Dermoscopy of a skin lesion; a male patient about 65 years old — 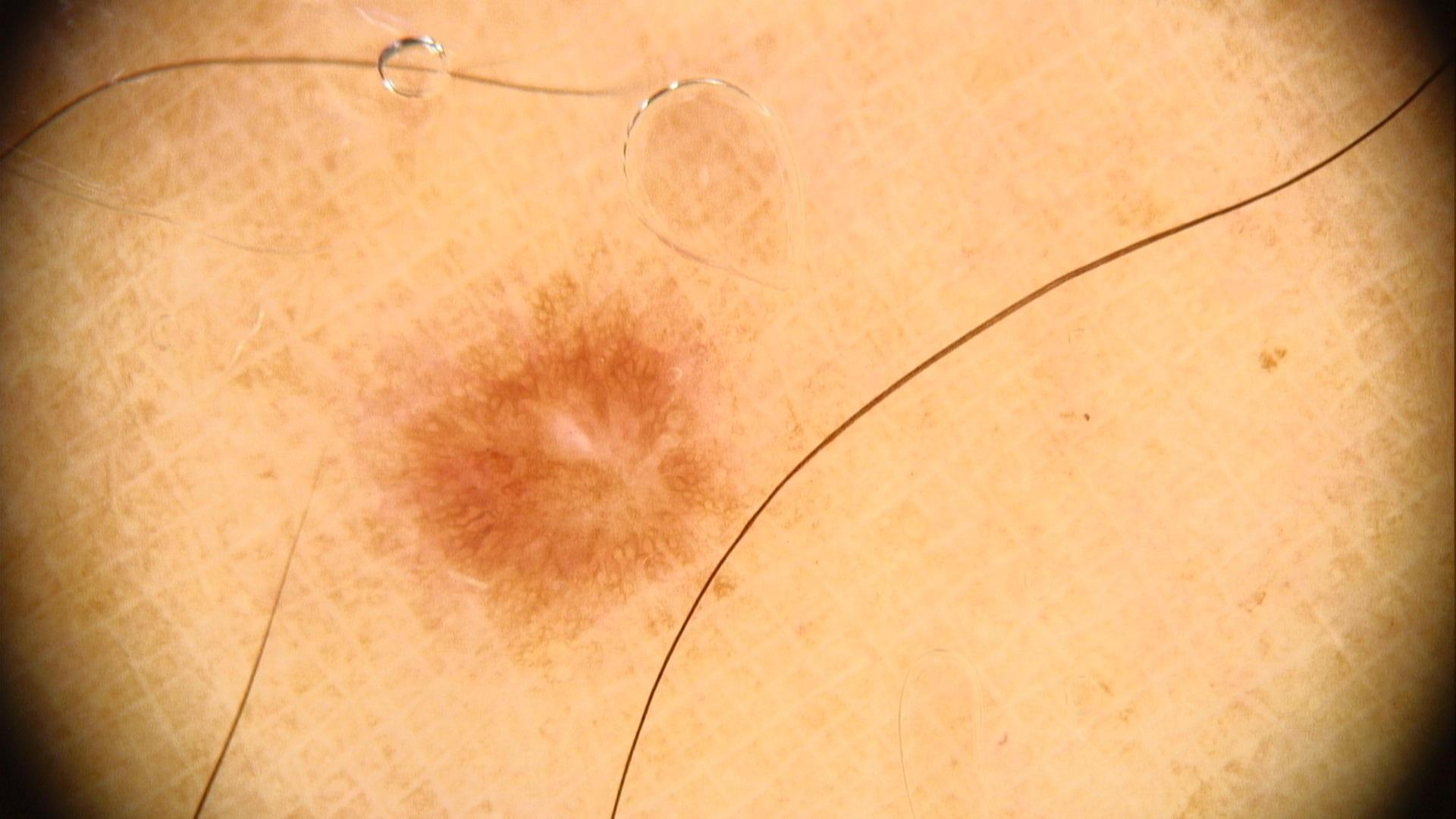anatomic site=a lower extremity | impression=Dermatofibroma.